A dermoscopic view of a skin lesion; a female patient, about 40 years old: 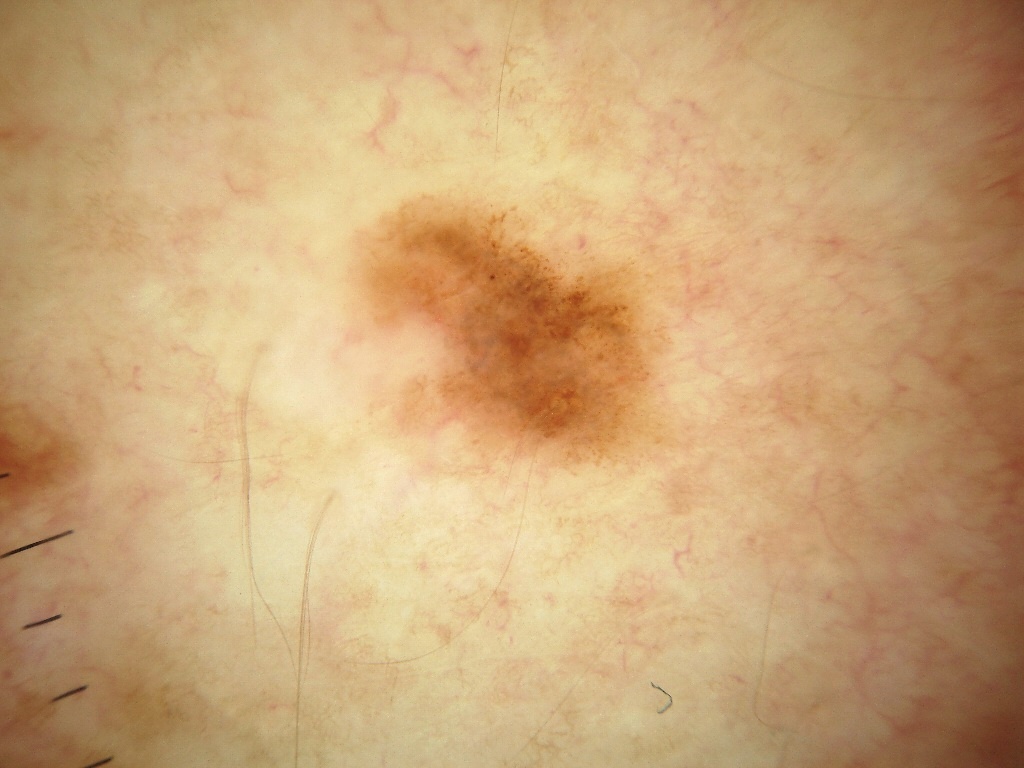Image and clinical context: With coordinates (x1, y1, x2, y2), the lesion is located at bbox=[318, 174, 703, 496]. Dermoscopy demonstrates globules. Conclusion: Consistent with a melanocytic nevus, a benign lesion.